A dermoscopy image of a single skin lesion: 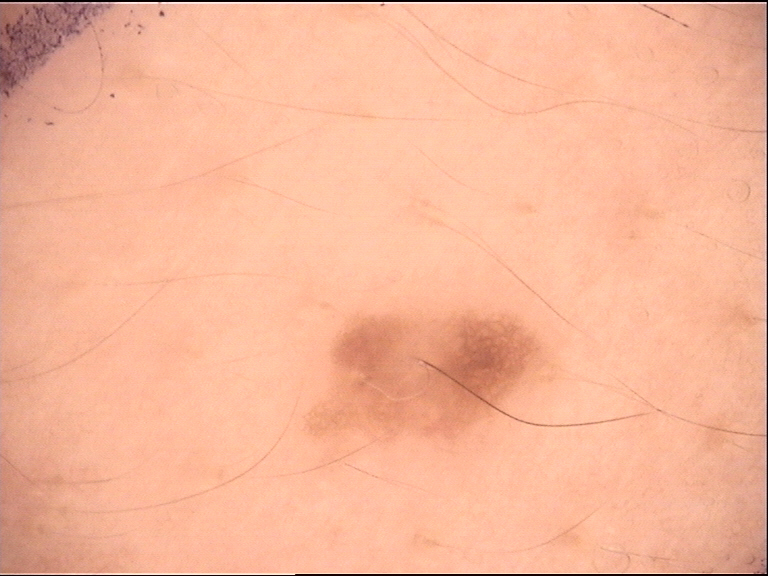The diagnostic label was a banal lesion — a dermal nevus.